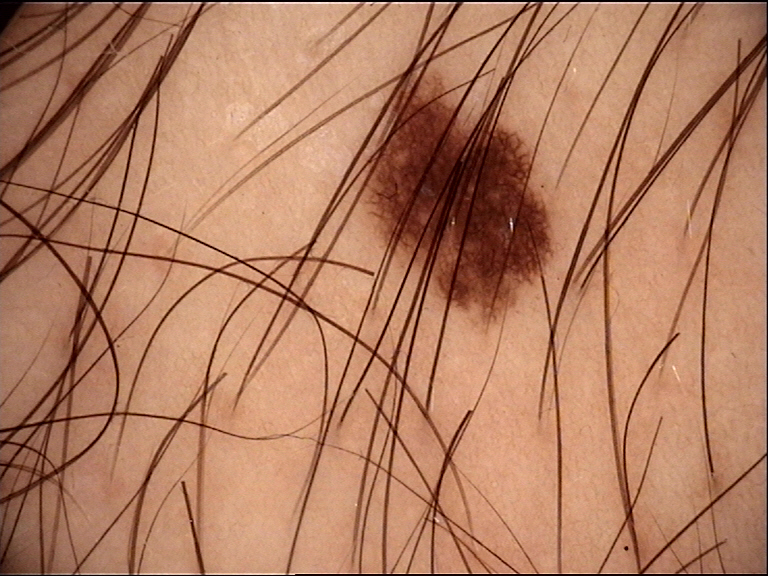Classified as a junctional nevus.